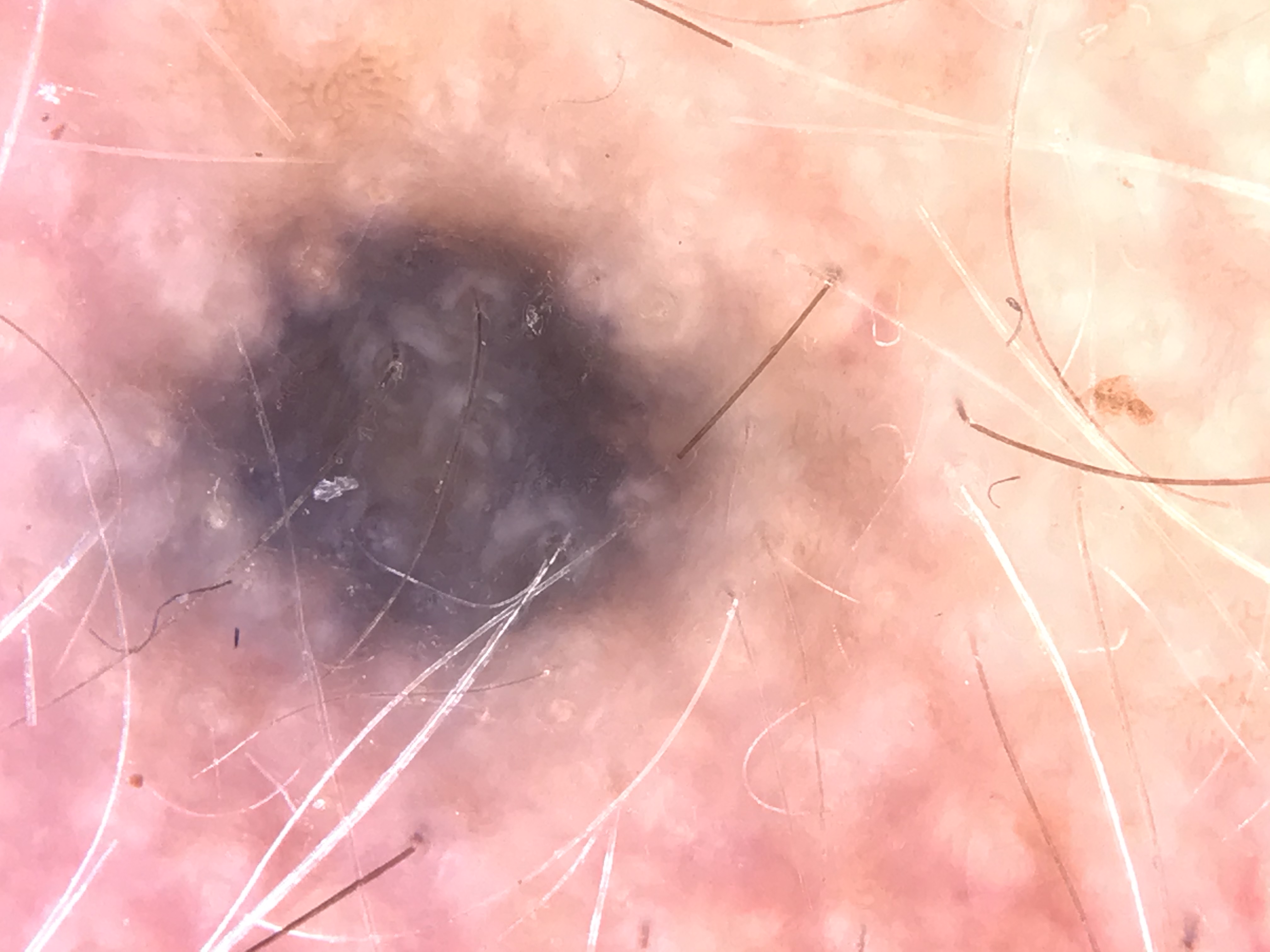The architecture is that of a banal, dermal lesion.
Consistent with a blue nevus.